A male subject 36 years of age; Fitzpatrick phototype IV; the chart records prior malignancy (patient or family); a clinical photograph showing a skin lesion:
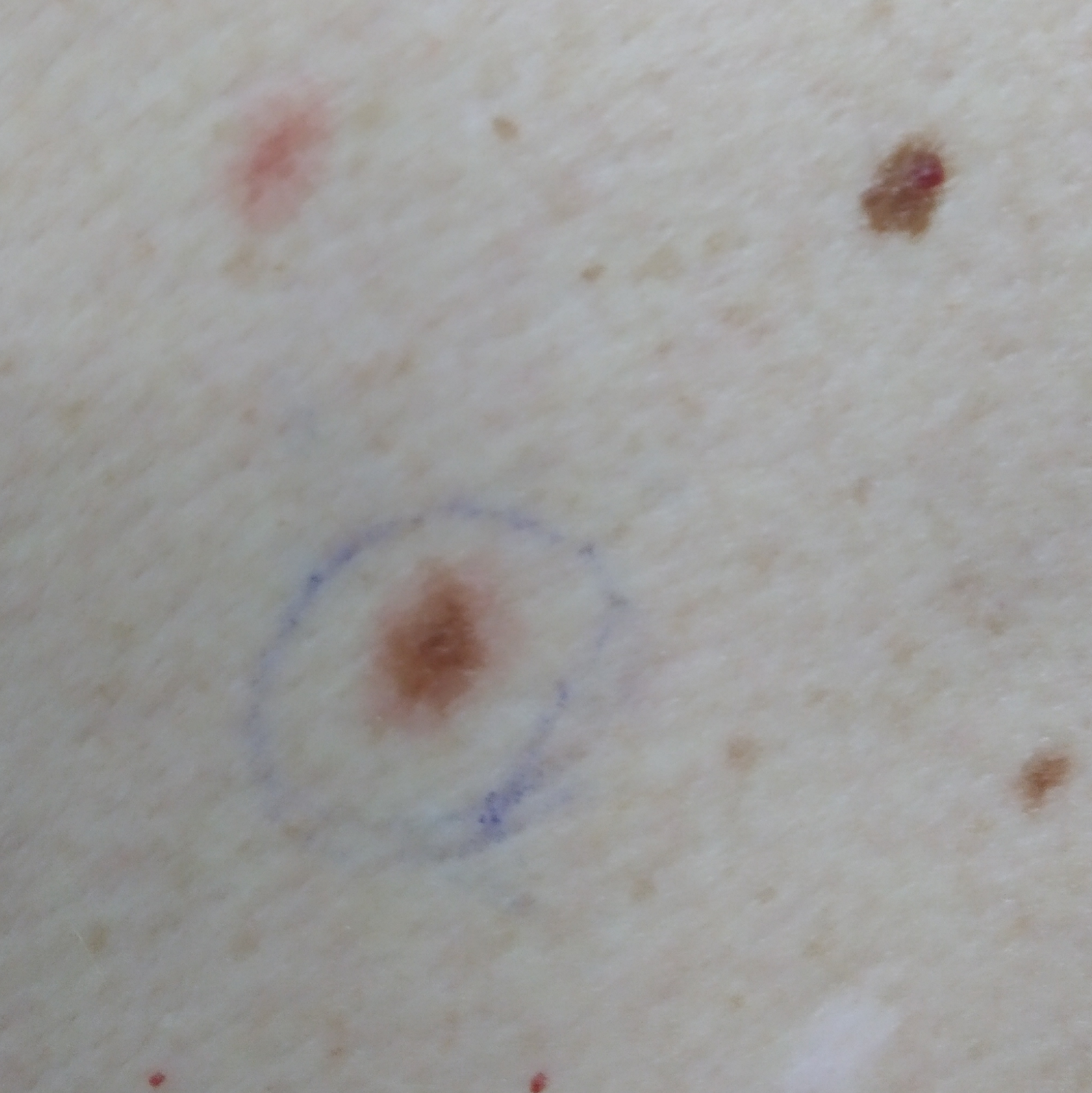Clinical context:
The lesion involves the back. The lesion measures approximately 7 × 4 mm. By the patient's account, the lesion itches.
Pathology:
The biopsy diagnosis was a nevus.